A dermoscopic close-up of a skin lesion: 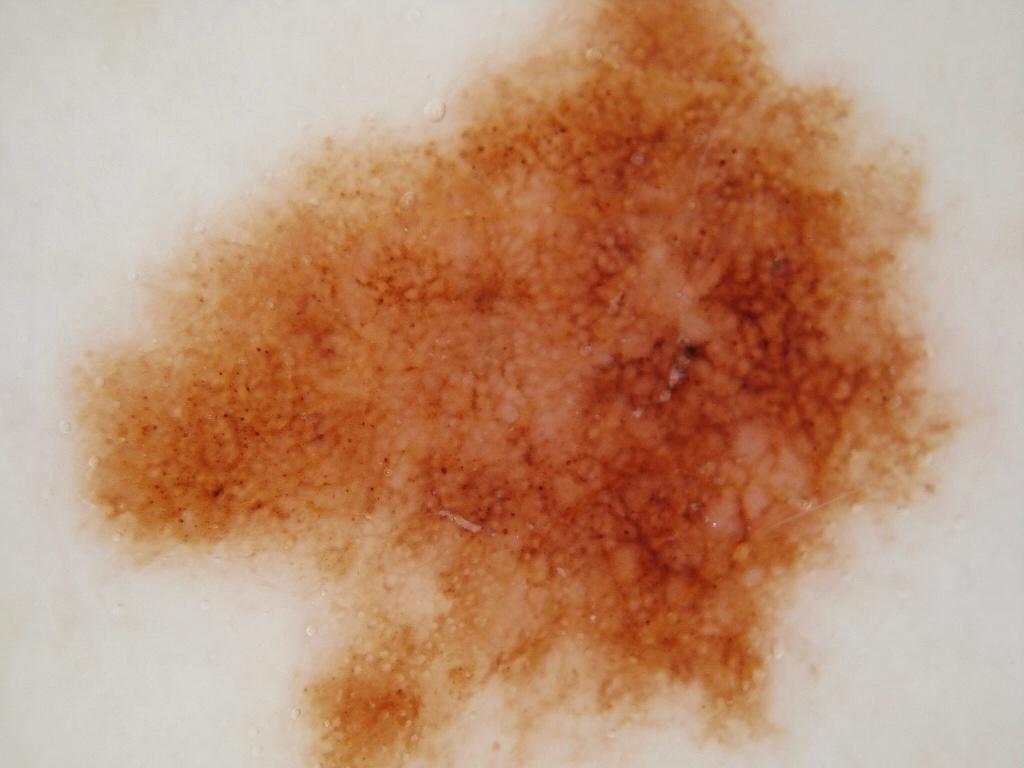Case summary:
Dermoscopy demonstrates pigment network, with no globules, milia-like cysts, negative network, or streaks. The lesion is bounded by x1=64, y1=0, x2=970, y2=763.
Diagnosis:
Histopathological examination showed a melanoma.